Dermoscopy of a skin lesion:
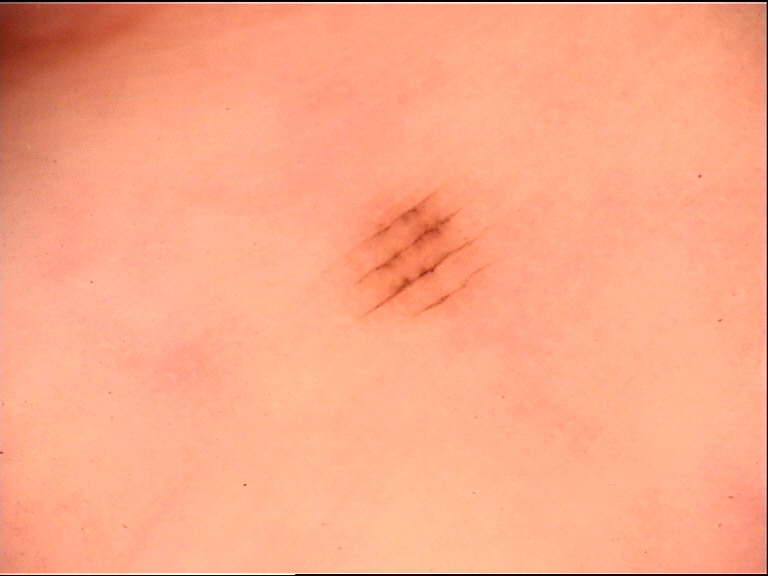Findings: This is a banal lesion. Impression: Labeled as an acral junctional nevus.